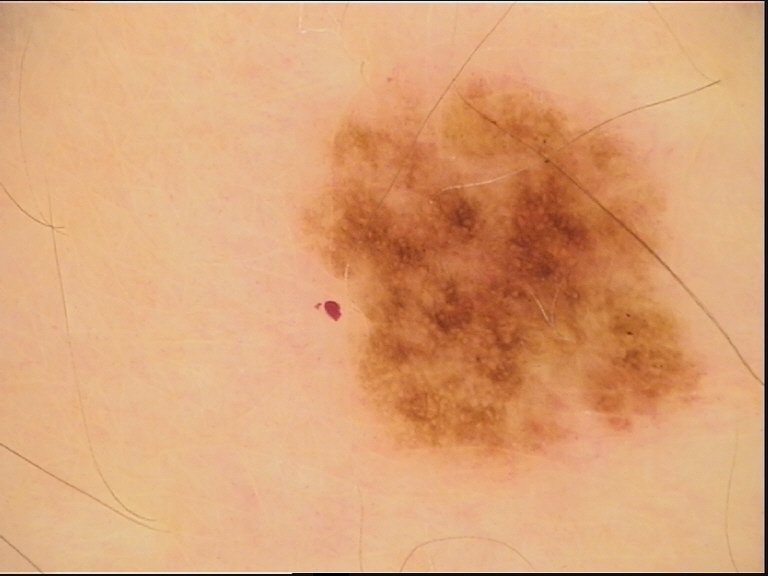A dermoscopic photograph of a skin lesion.
The diagnosis was a benign lesion — a dysplastic junctional nevus.